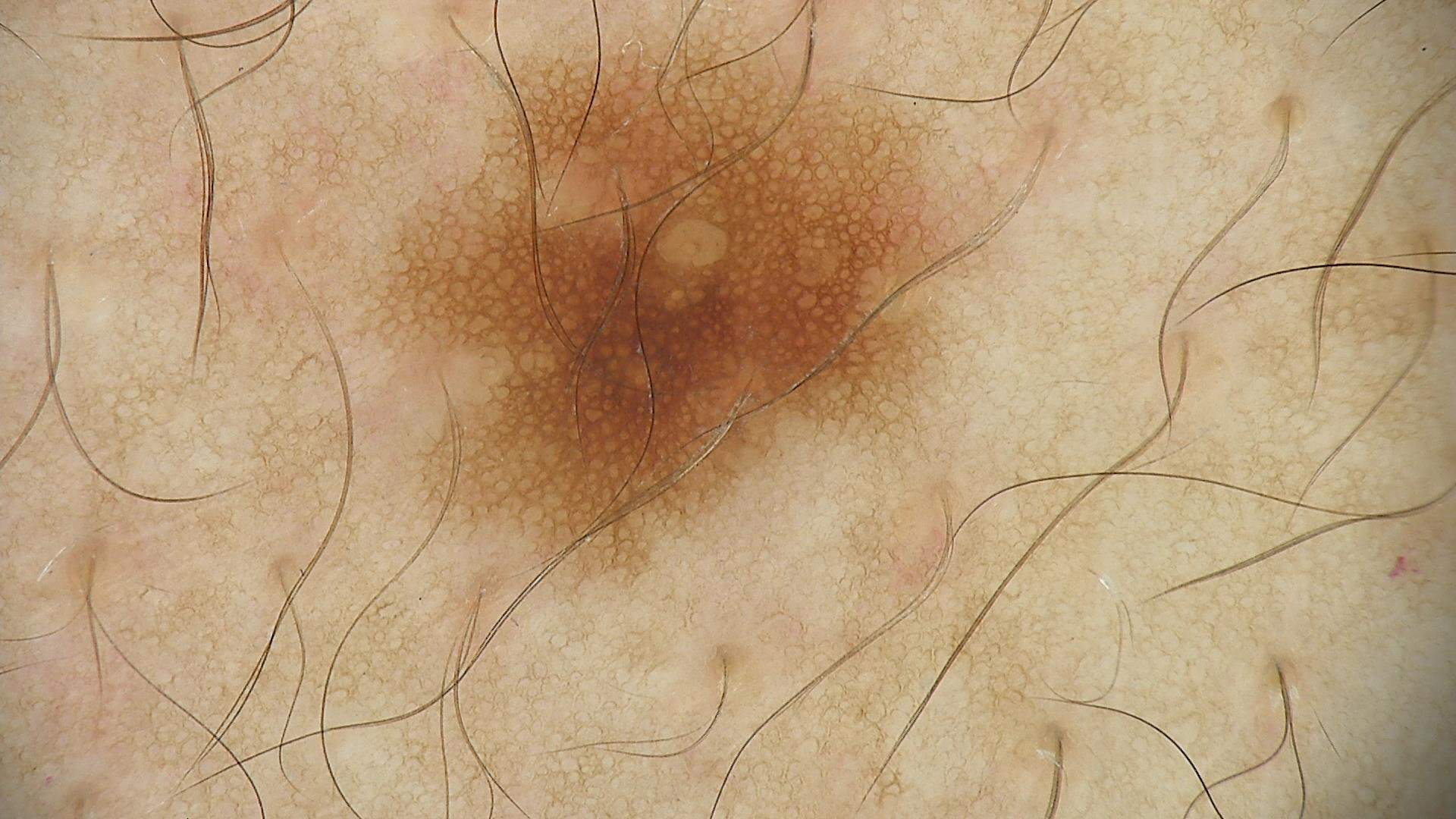{
  "diagnosis": {
    "name": "dysplastic junctional nevus",
    "code": "jd",
    "malignancy": "benign",
    "super_class": "melanocytic",
    "confirmation": "expert consensus"
  }
}